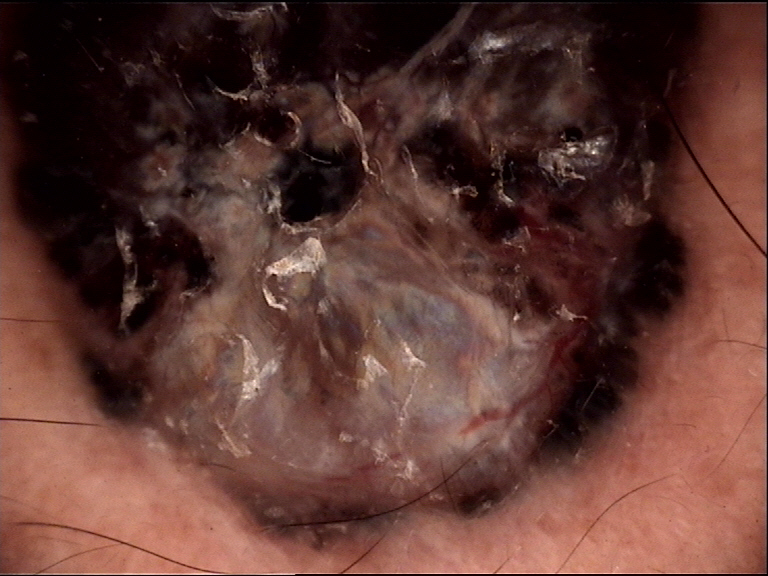Histopathologically confirmed as a melanoma.